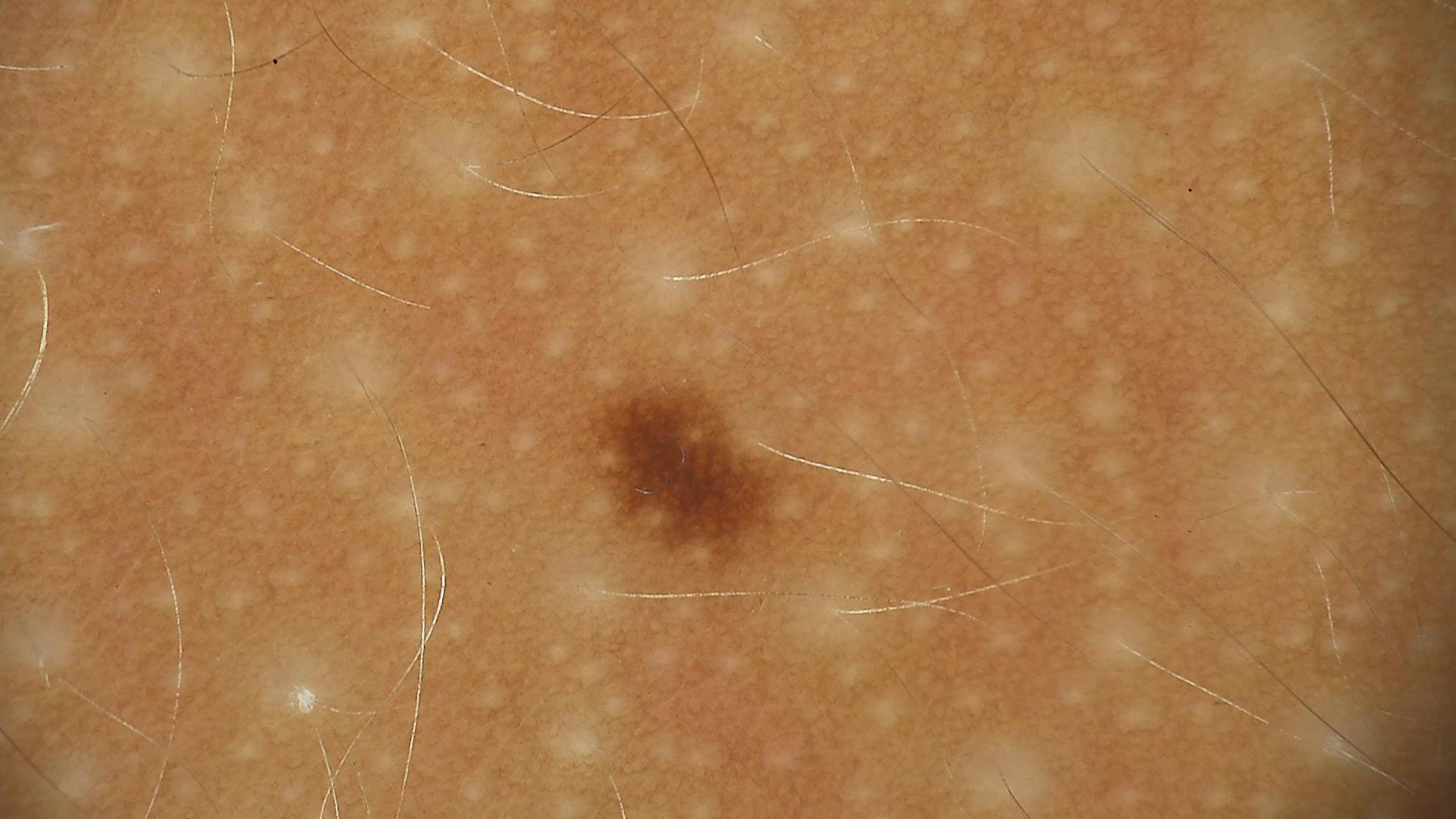Case:
Dermoscopy of a skin lesion.
Impression:
The diagnosis was a dysplastic junctional nevus.